The patient is a male approximately 15 years of age. Dermoscopy of a skin lesion — 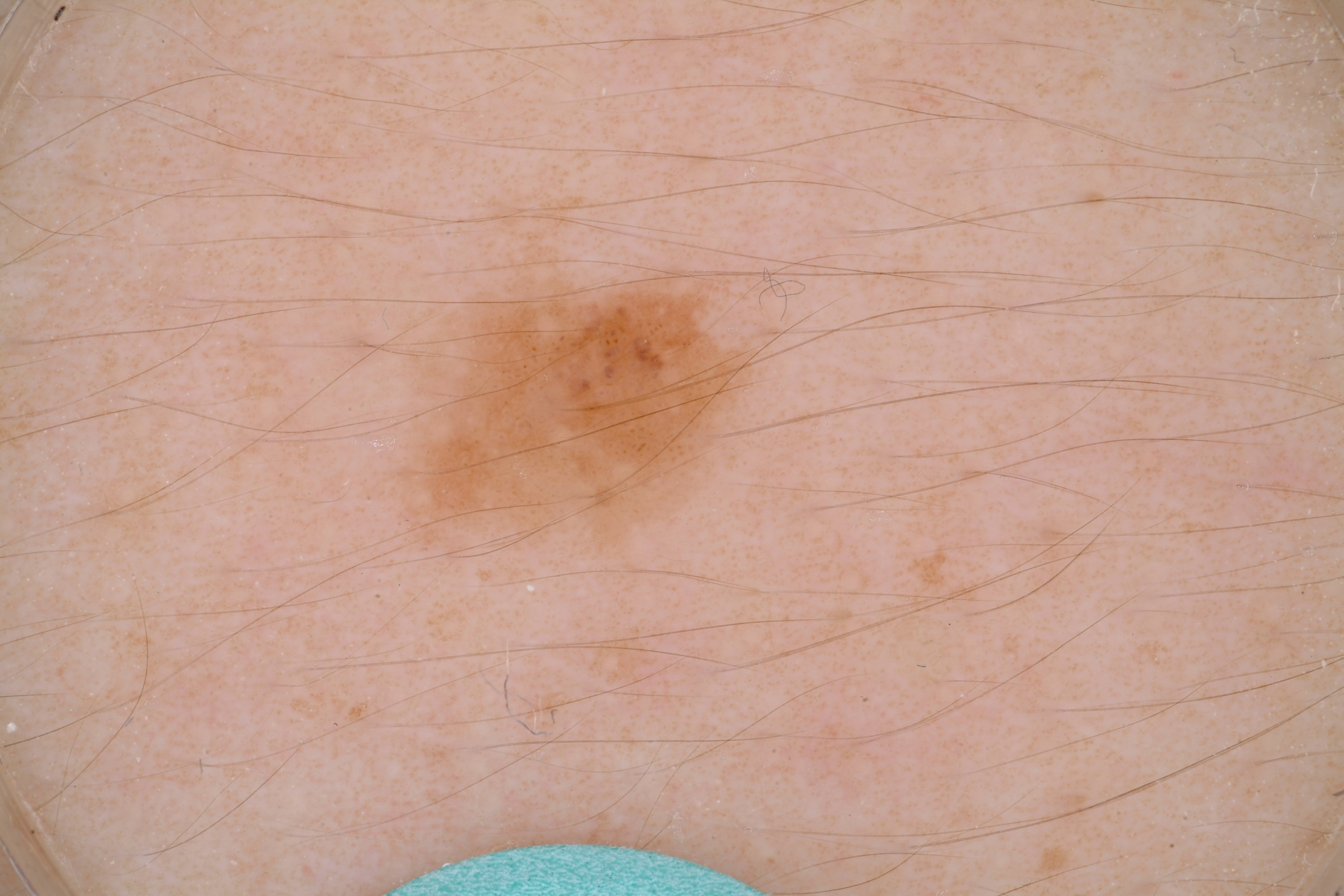<record>
  <lesion_extent>small</lesion_extent>
  <lesion_location>
    <bbox_xyxy>397, 267, 759, 558</bbox_xyxy>
  </lesion_location>
  <dermoscopic_features>
    <present>globules</present>
    <absent>negative network, milia-like cysts, pigment network, streaks</absent>
  </dermoscopic_features>
  <diagnosis>
    <name>melanocytic nevus</name>
    <malignancy>benign</malignancy>
    <lineage>melanocytic</lineage>
    <provenance>clinical</provenance>
  </diagnosis>
</record>